Close-up view · no constitutional symptoms were reported · reported duration is one to four weeks · the subject is a male aged 40–49 · texture is reported as raised or bumpy and flat · located on the front of the torso · the contributor notes itching and bothersome appearance: 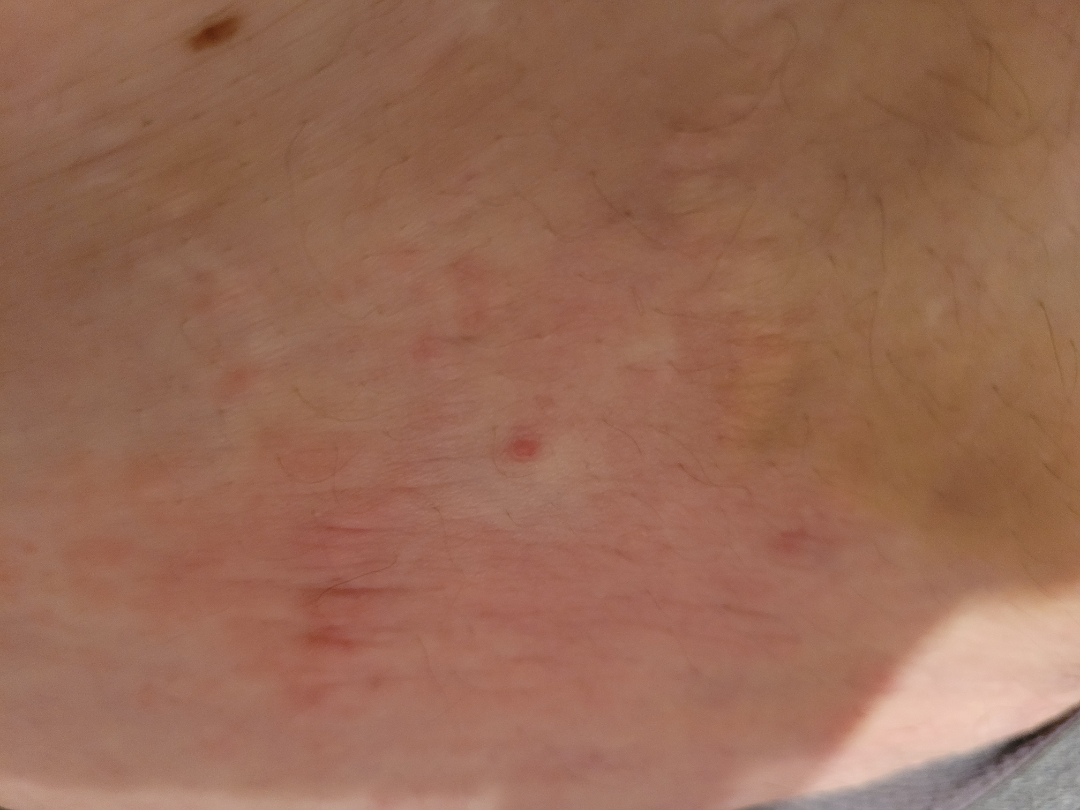Q: Could the case be diagnosed?
A: could not be assessed